A dermoscopic close-up of a skin lesion.
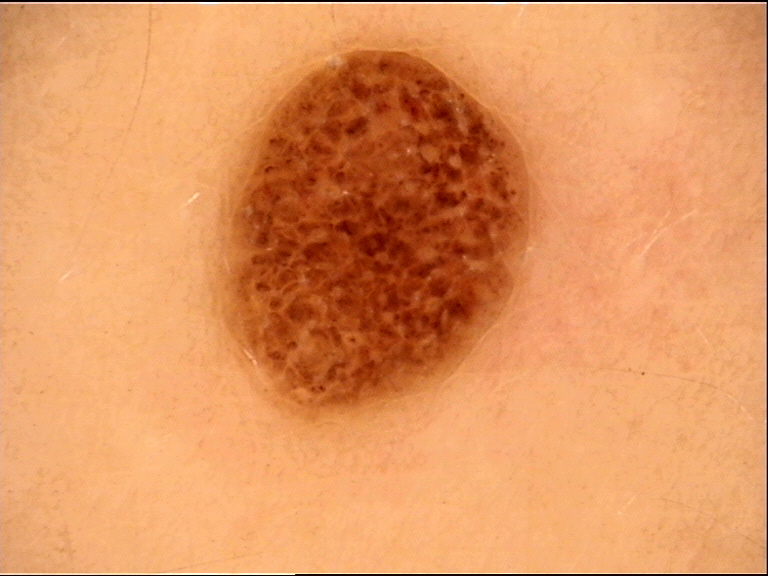classification — banal
diagnosis — compound nevus (expert consensus)